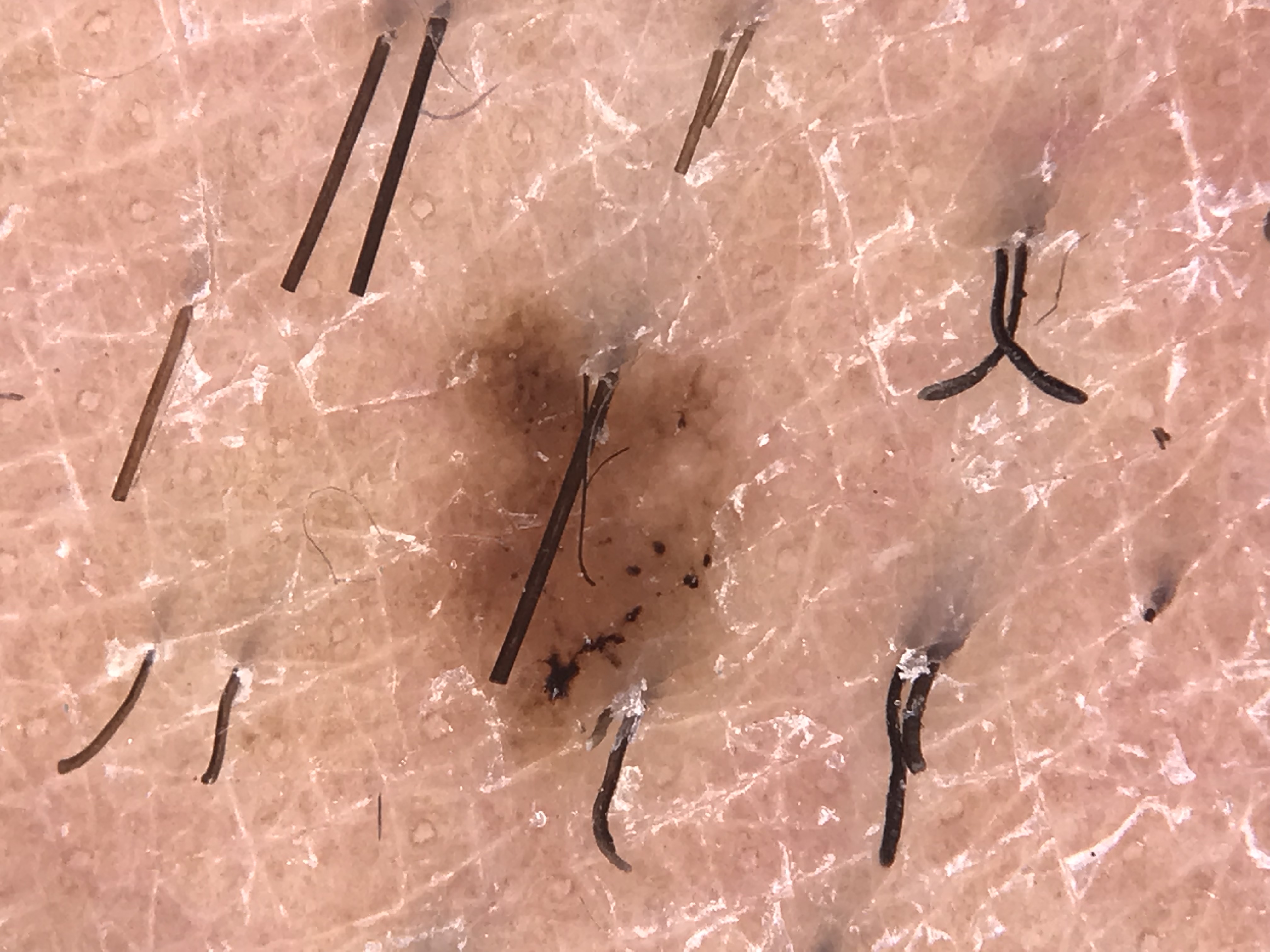Conclusion:
Labeled as a dysplastic junctional nevus.